A subject 82 years of age · a clinical photograph of a skin lesion.
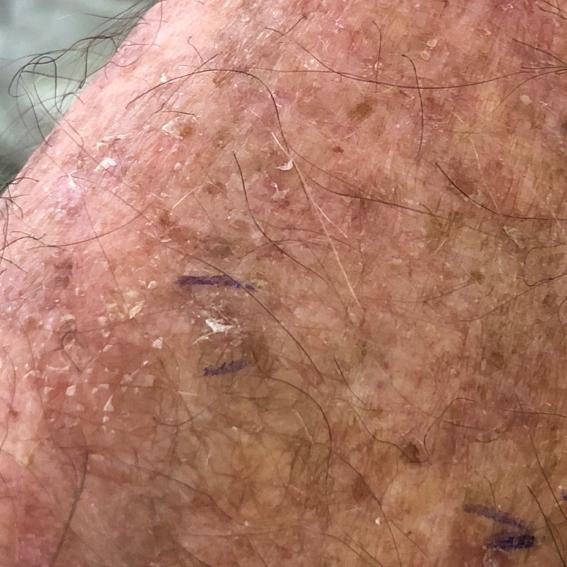Q: What is the anatomic site?
A: a forearm
Q: Any reported symptoms?
A: itching / no change in appearance, no elevation
Q: What was the clinical impression?
A: actinic keratosis (clinical consensus)